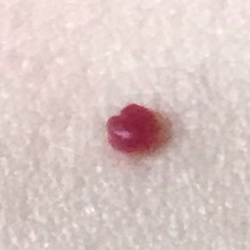Case summary:
The patient describes that the lesion is elevated.
Conclusion:
Consistent with a nevus.